This image was taken at a distance. The leg is involved.
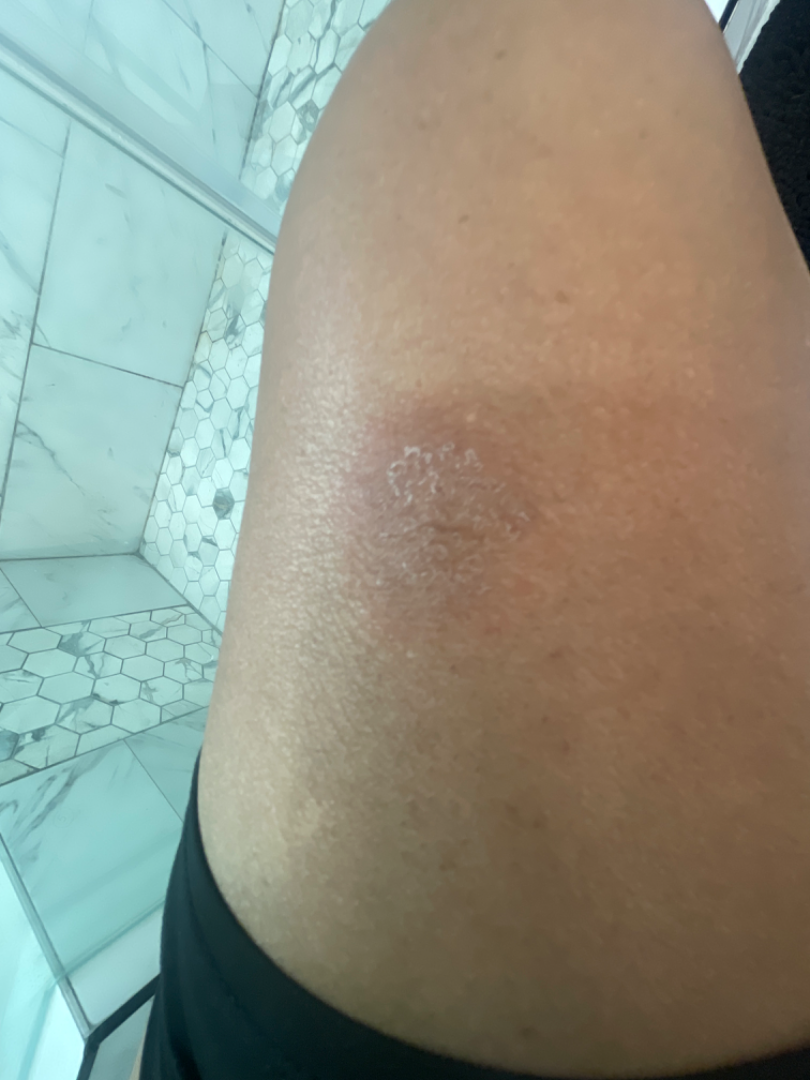Q: What symptoms does the patient report?
A: enlargement
Q: Any systemic symptoms?
A: none reported
Q: What is the dermatologist's impression?
A: Eczema (considered); Impetigo (considered); Psoriasis (considered)